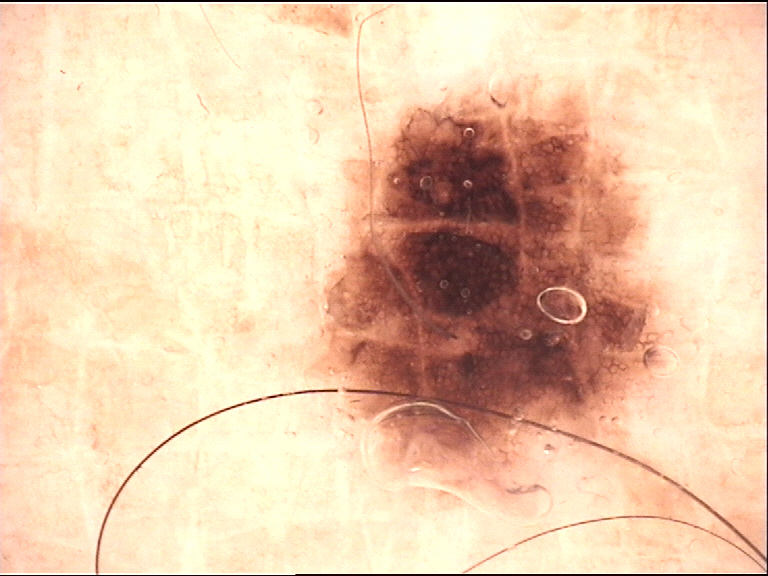{"image": "dermoscopy", "diagnosis": {"name": "dysplastic compound nevus", "code": "cd", "malignancy": "benign", "super_class": "melanocytic", "confirmation": "expert consensus"}}